This is a close-up image. The patient described the issue as a rash. The affected area is the leg and arm. Male contributor, age 18–29. The patient notes the condition has been present for less than one week — 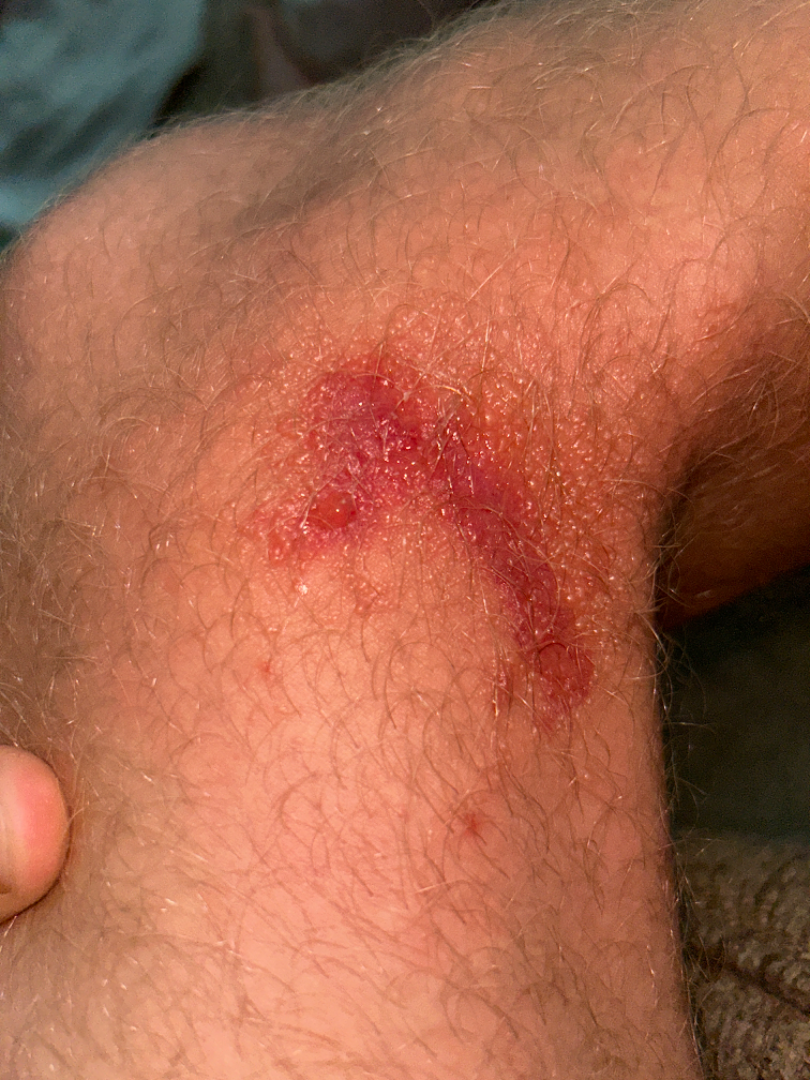Findings:
– assessment: favoring Allergic Contact Dermatitis; the differential also includes Abrasion and/or friction burn of lower limb without infection; less probable is Urticaria